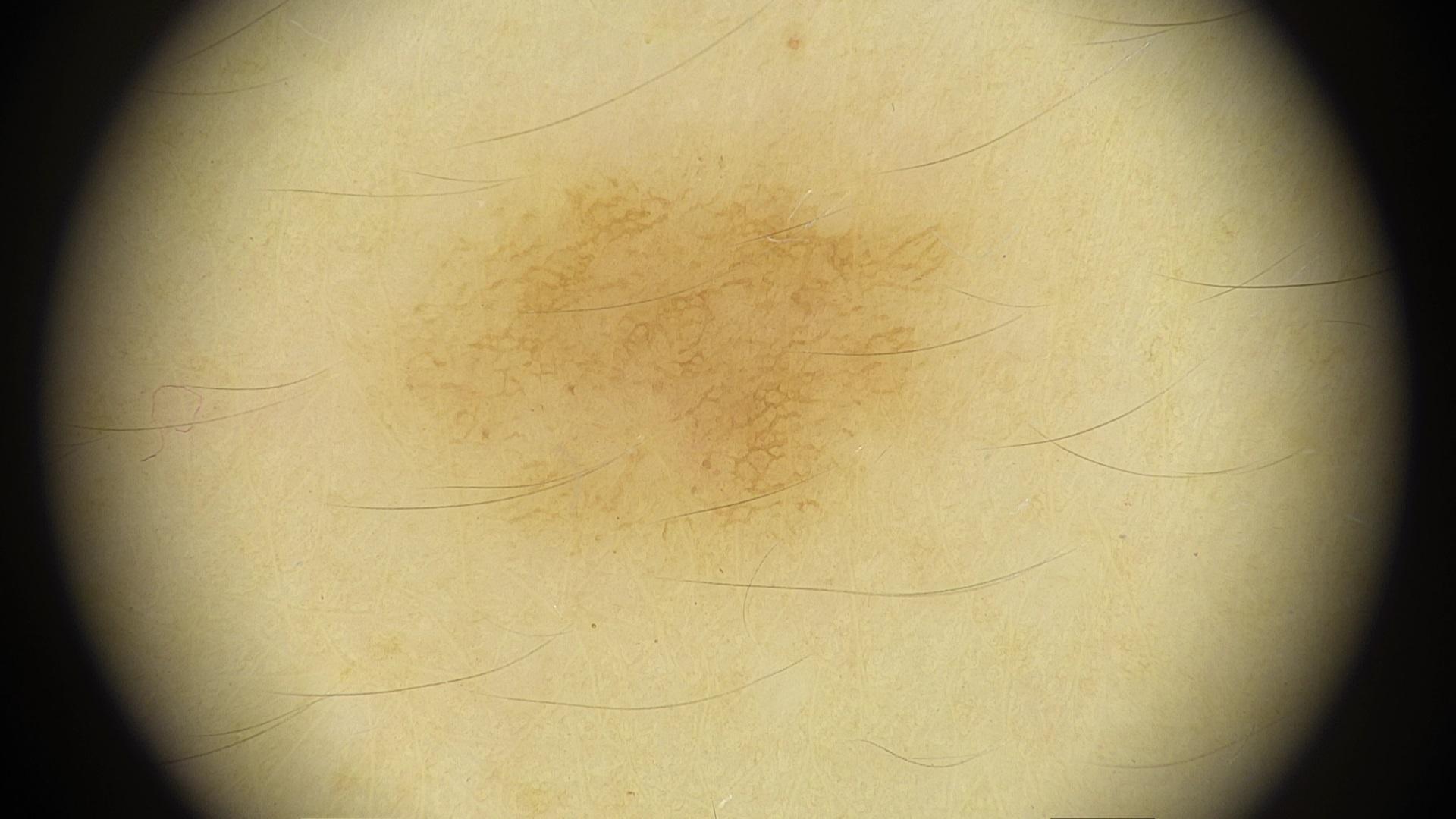Q: What is the melanoma history?
A: no previous melanoma and no first-degree relative with melanoma
Q: What Fitzpatrick skin type was recorded?
A: II
Q: What are the patient's age and sex?
A: female, in their mid- to late 30s
Q: What is the imaging modality?
A: dermoscopic image
Q: Where is the lesion located?
A: the trunk (the posterior trunk)
Q: What was the clinical impression?
A: Nevus